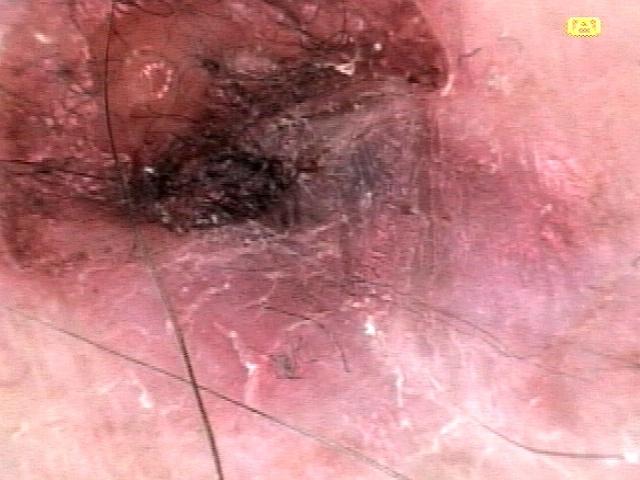The clinical impression was a vascular lesion.